A close-up photograph: 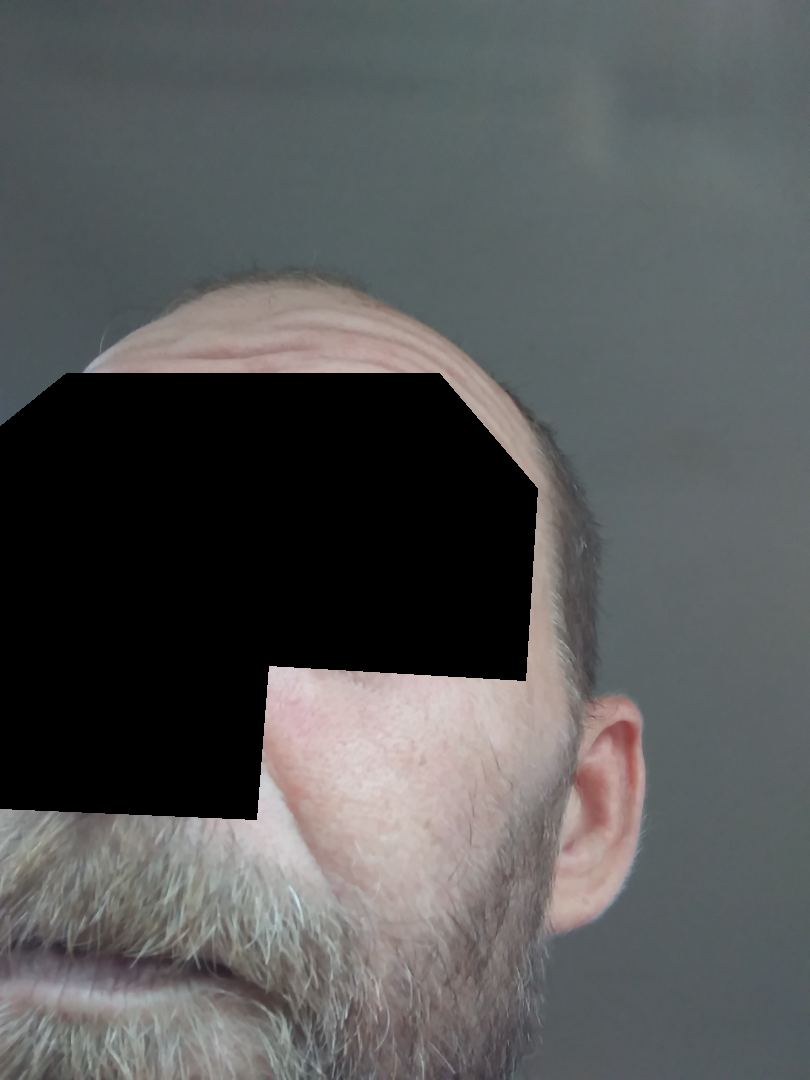The reviewing dermatologist did not identify a discernible skin condition.